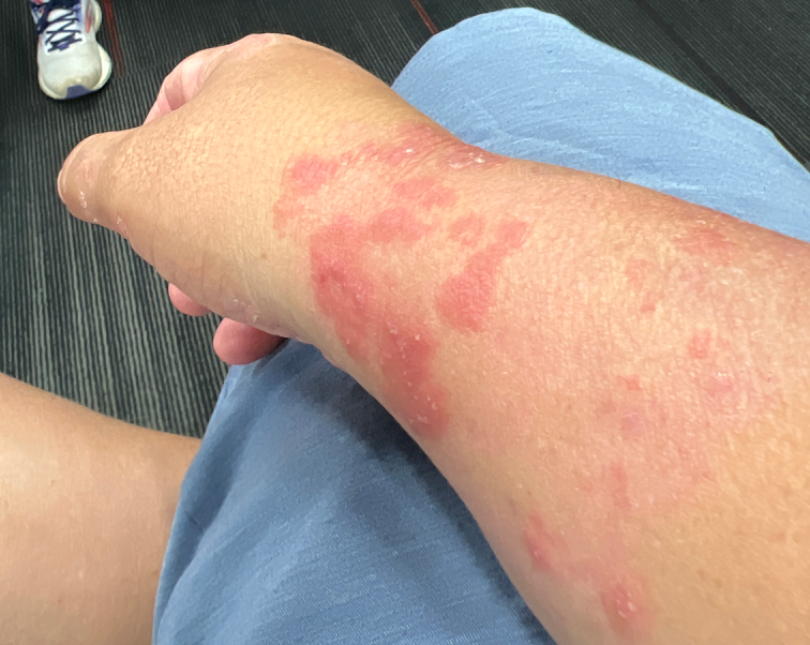{
  "shot_type": "at an angle",
  "differential": {
    "leading": [
      "Acute dermatitis, NOS"
    ]
  }
}